The photo was captured at an angle. Located on the arm. The patient is 50–59, male — 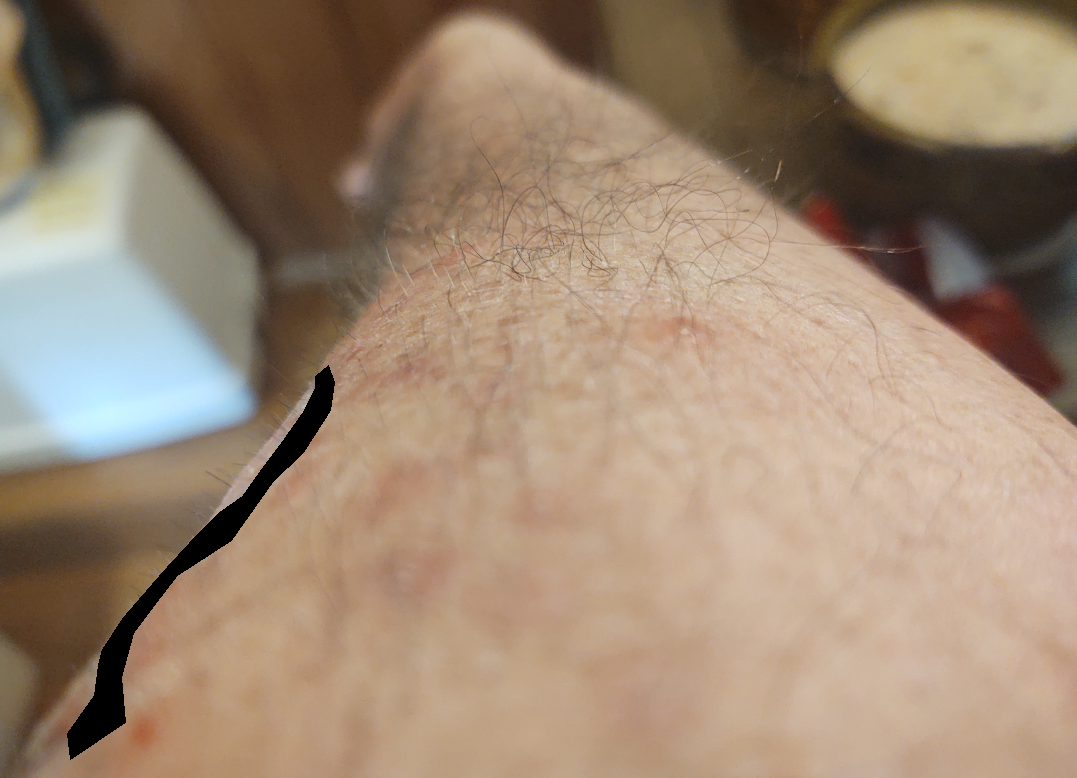dermatologist impression = the favored diagnosis is Folliculitis; an alternative is Irritant Contact Dermatitis.